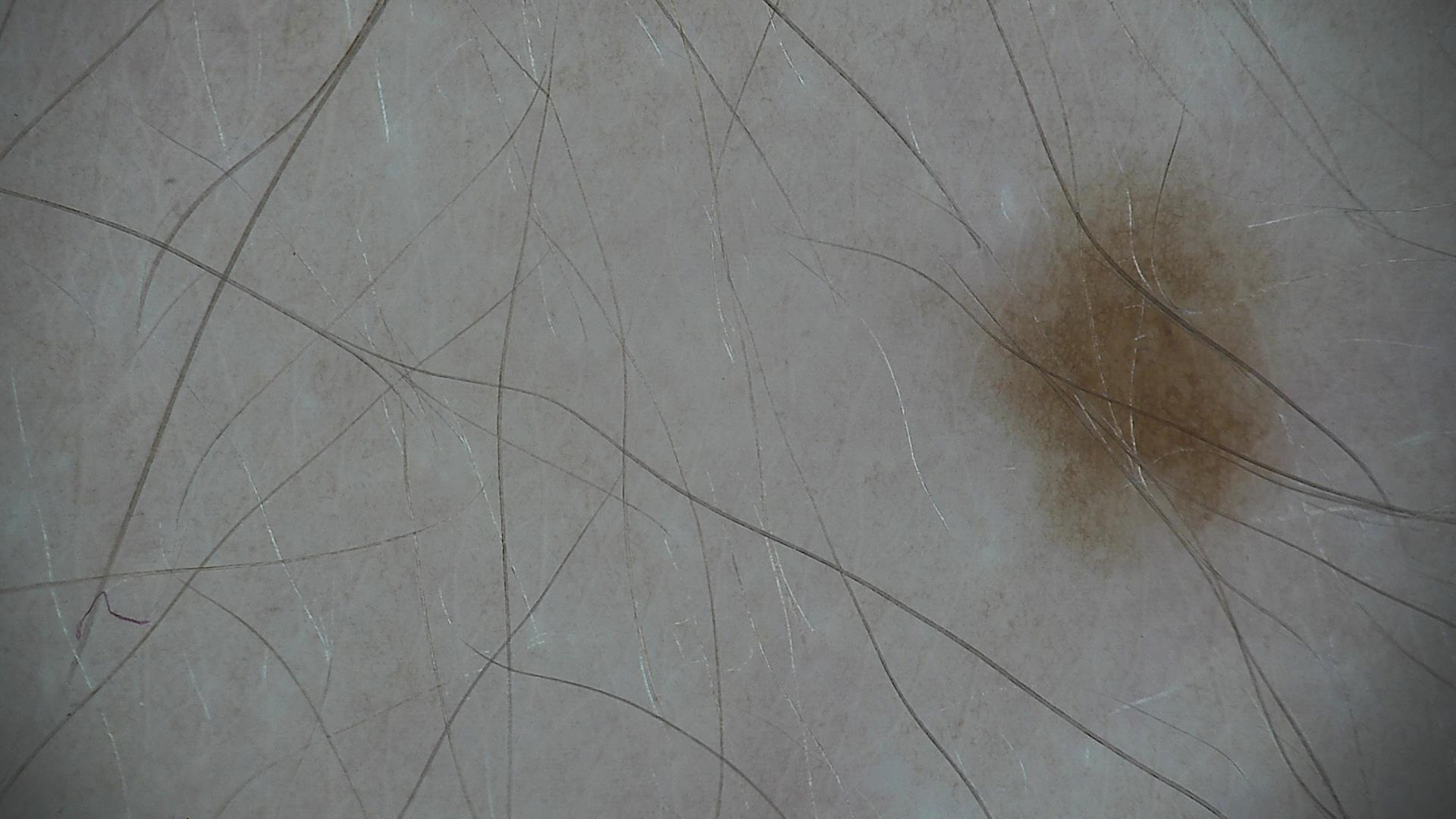{
  "image": "dermoscopy",
  "diagnosis": {
    "name": "dysplastic junctional nevus",
    "code": "jd",
    "malignancy": "benign",
    "super_class": "melanocytic",
    "confirmation": "expert consensus"
  }
}